Self-categorized by the patient as a growth or mole · the lesion is described as raised or bumpy · skin tone: lay graders estimated 2 on the Monk Skin Tone · the lesion involves the leg · the photo was captured at a distance · the patient is female · present for less than one week · no associated systemic symptoms reported.
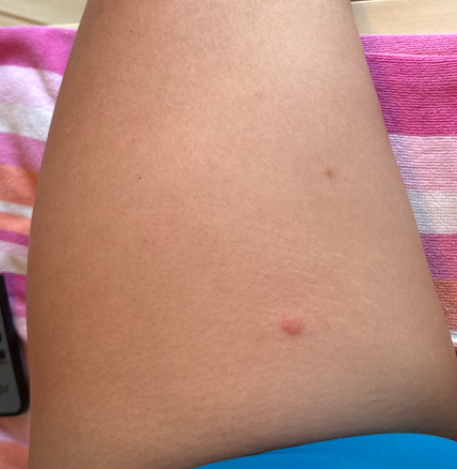assessment: ungradable on photographic review